An image taken at a distance · the lesion involves the arm — 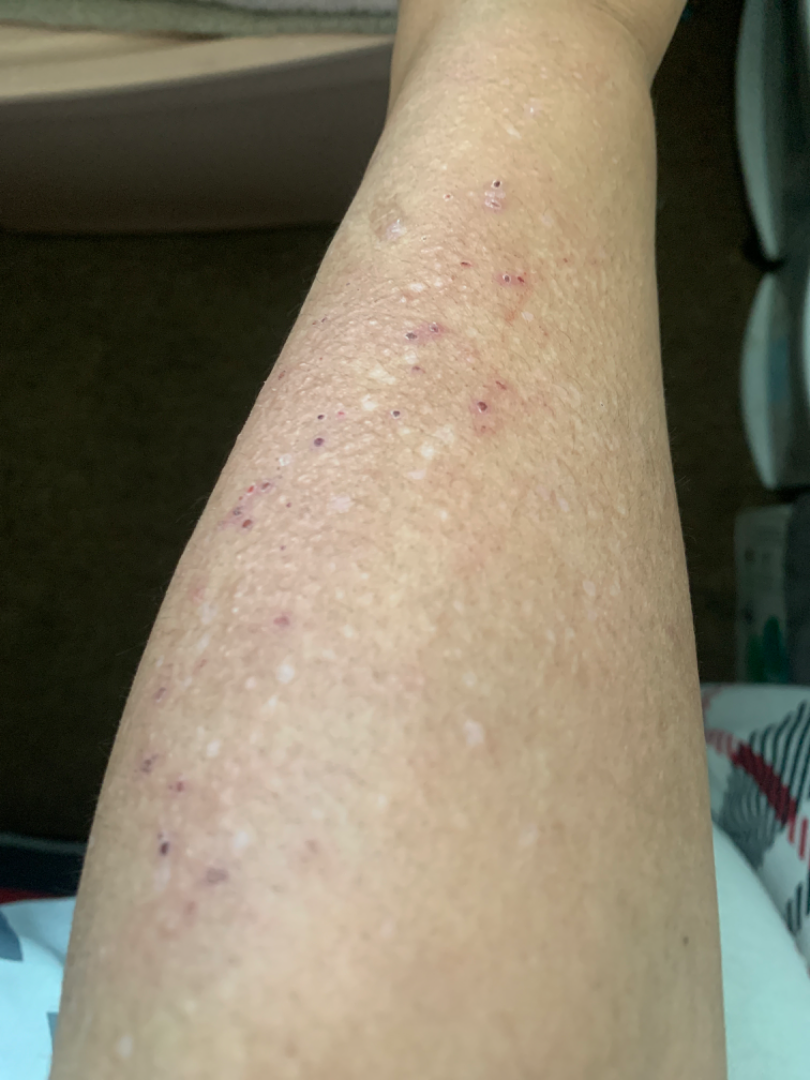Q: What was the assessment?
A: ungradable on photographic review
Q: Reported symptoms?
A: itching
Q: How does the patient describe it?
A: a rash
Q: Constitutional symptoms?
A: none reported
Q: When did this start?
A: less than one week
Q: How does the lesion feel?
A: rough or flaky, flat and raised or bumpy